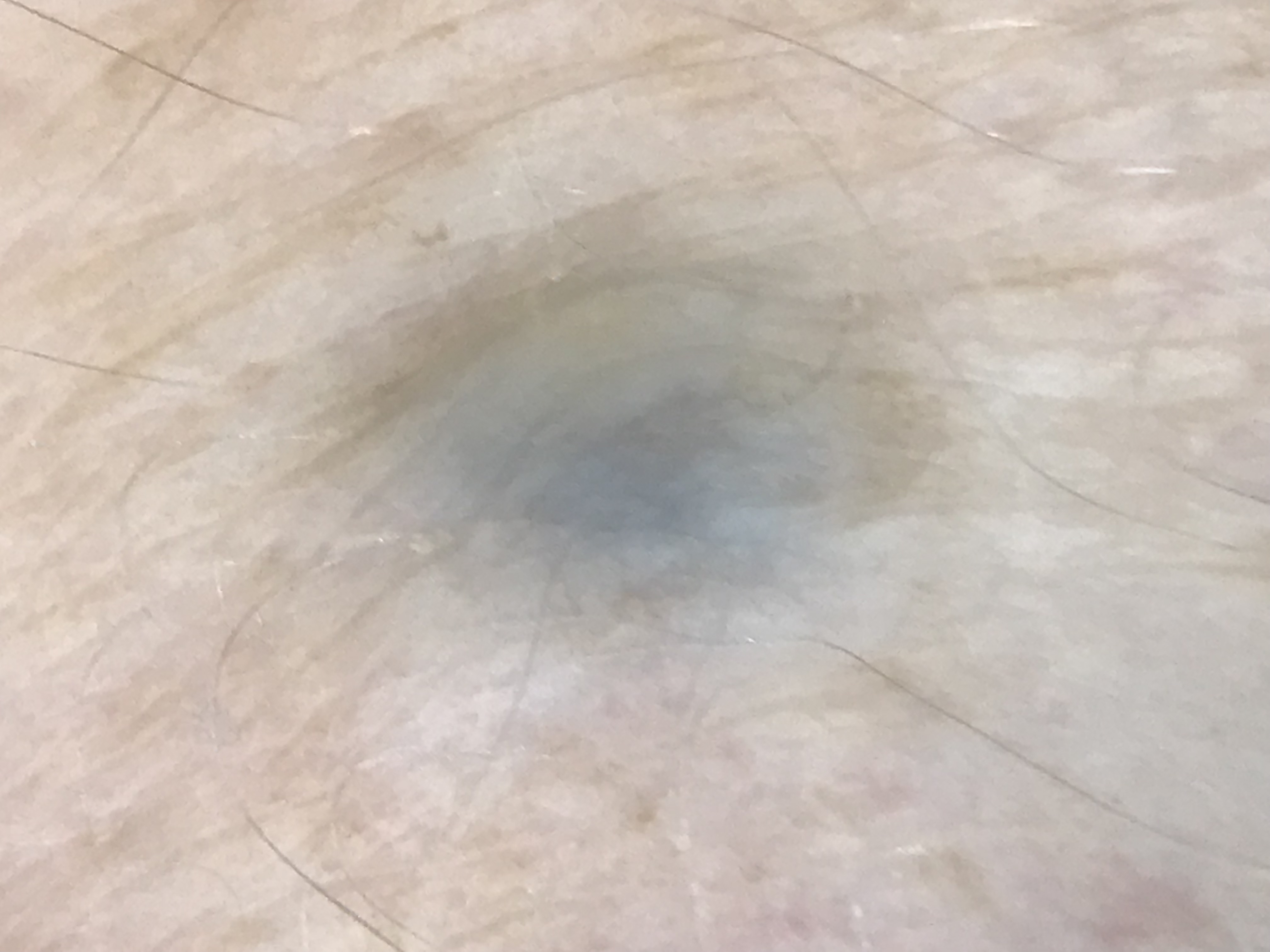Dermoscopy of a skin lesion.
Diagnosed as a banal lesion — a blue nevus.